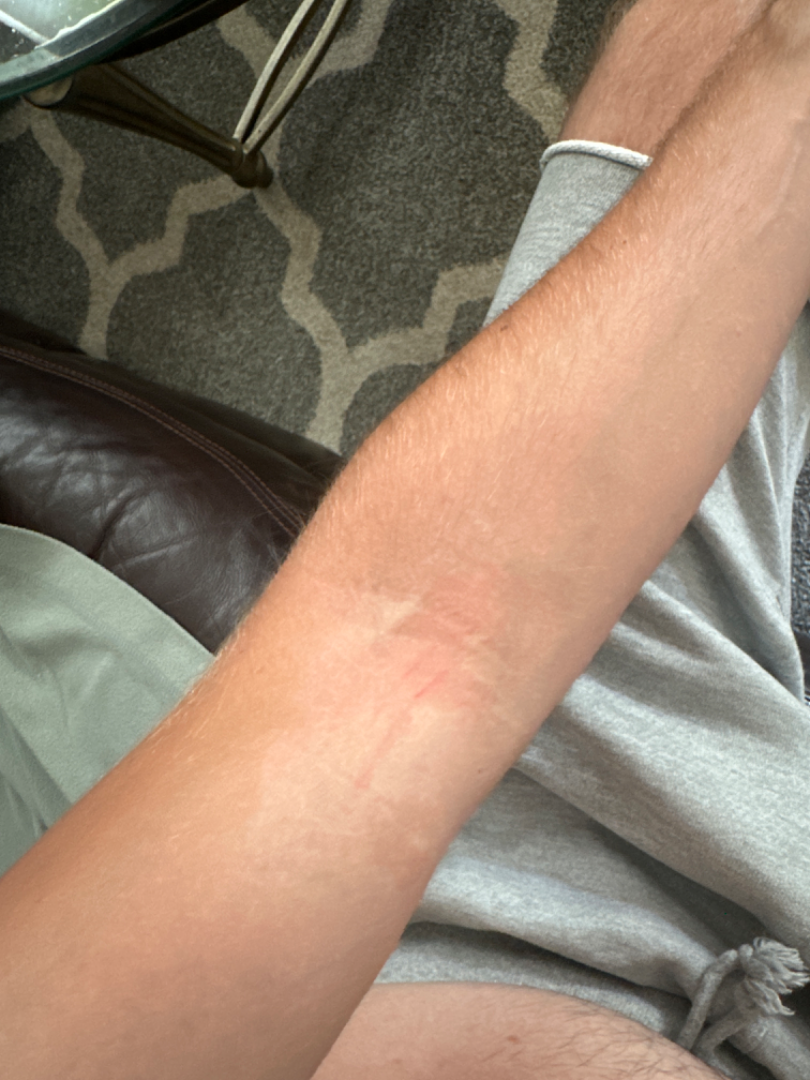<summary>
  <assessment>ungradable on photographic review</assessment>
  <shot_type>close-up</shot_type>
  <texture>raised or bumpy</texture>
  <duration>more than five years</duration>
  <patient_category>skin that appeared healthy to them</patient_category>
  <body_site>arm, head or neck</body_site>
  <symptoms>enlargement, burning, itching</symptoms>
</summary>